The patient indicates the condition has been present for less than one week; the affected area is the leg; the patient indicates the lesion is raised or bumpy and fluid-filled; self-categorized by the patient as a rash; the photograph was taken at an angle — 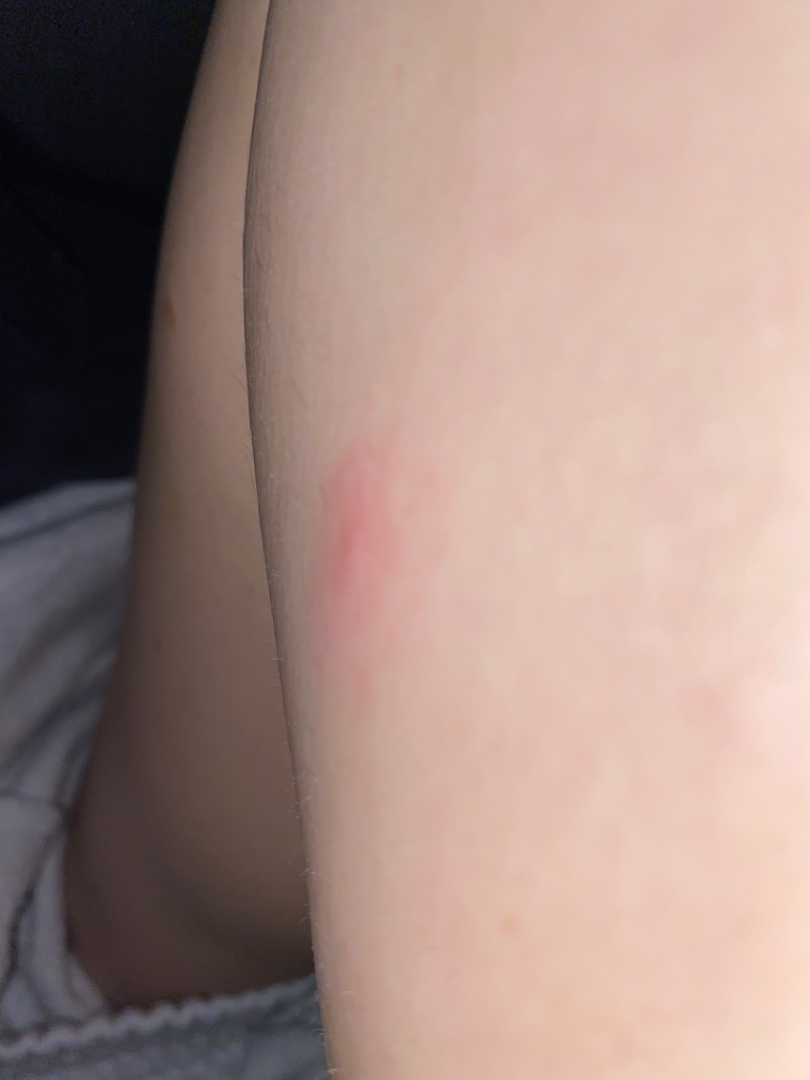assessment: ungradable on photographic review